The arm and head or neck are involved. The photograph is a close-up of the affected area. The patient is 18–29, male.
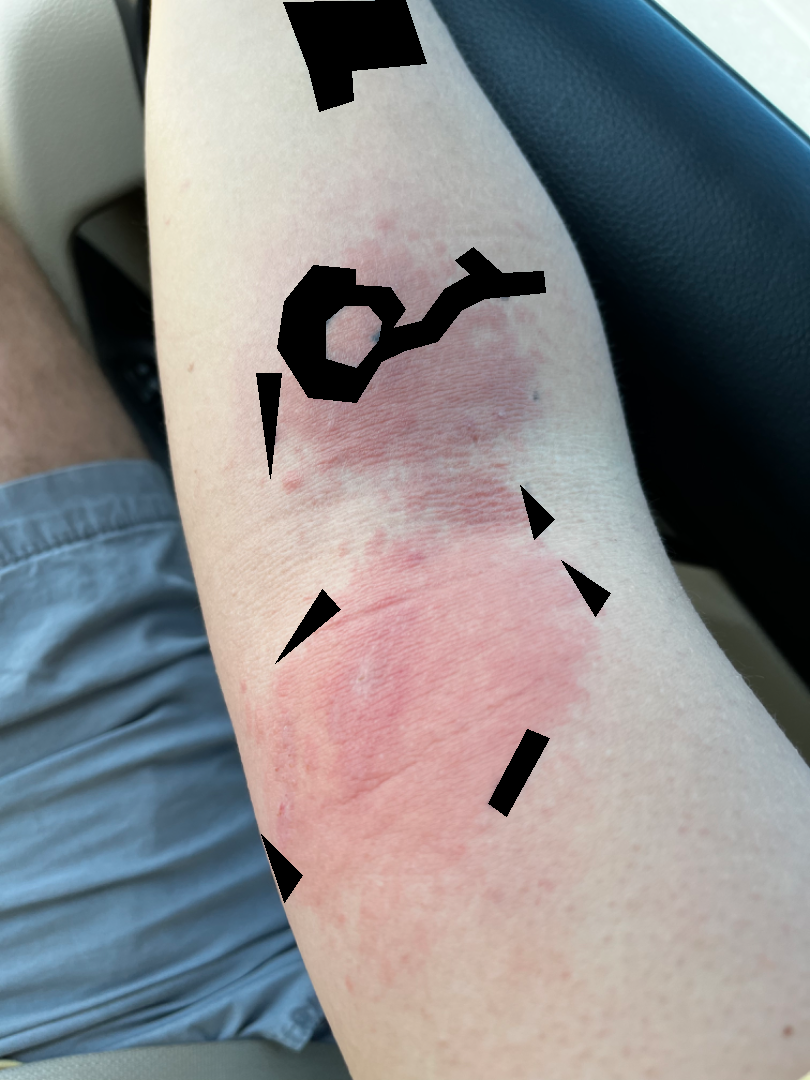The leading consideration is Allergic Contact Dermatitis; the differential also includes Urticaria; also raised was Insect Bite.